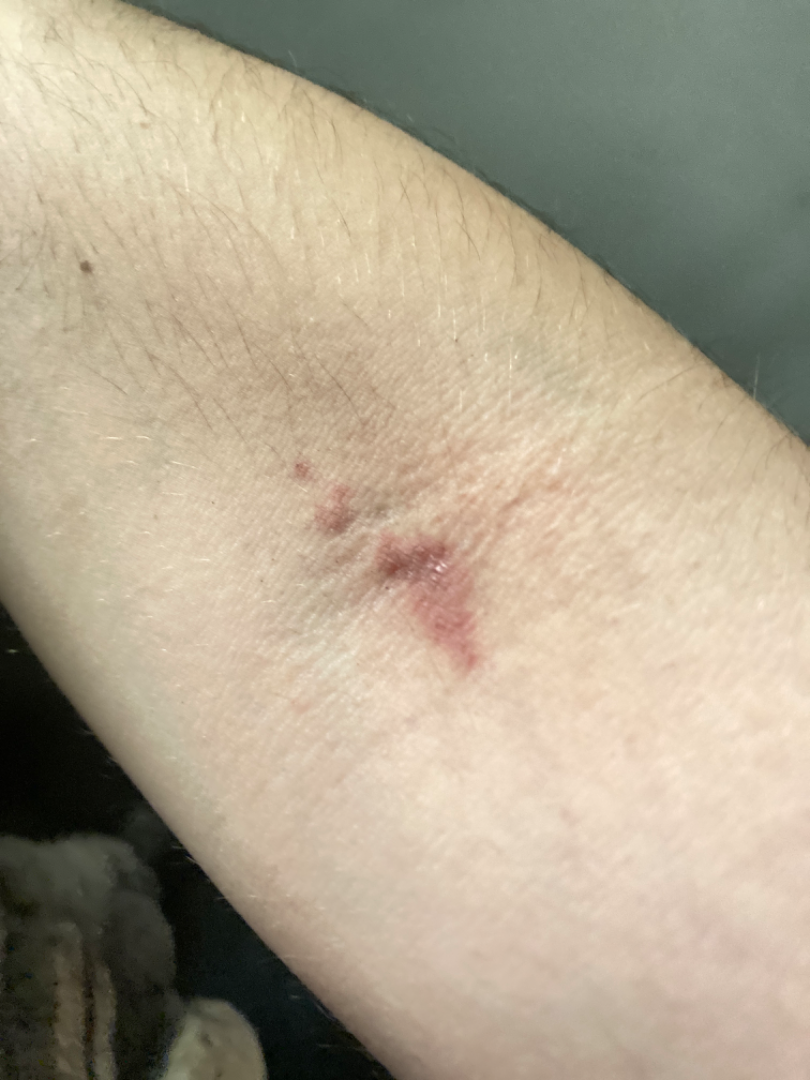Background:
The contributor notes the lesion is raised or bumpy, fluid-filled and rough or flaky. The lesion is associated with pain, darkening, bothersome appearance, enlargement, burning, itching and bleeding. Present for less than one week. The affected area is the arm. Fitzpatrick II; lay reviewers estimated Monk Skin Tone 2–3. The patient described the issue as a rash. This is a close-up image.
Findings:
Reviewed remotely by one dermatologist: pathergy and Kaposi's sarcoma of skin were considered with similar weight; a remote consideration is Abrasion, scrape, or scab.